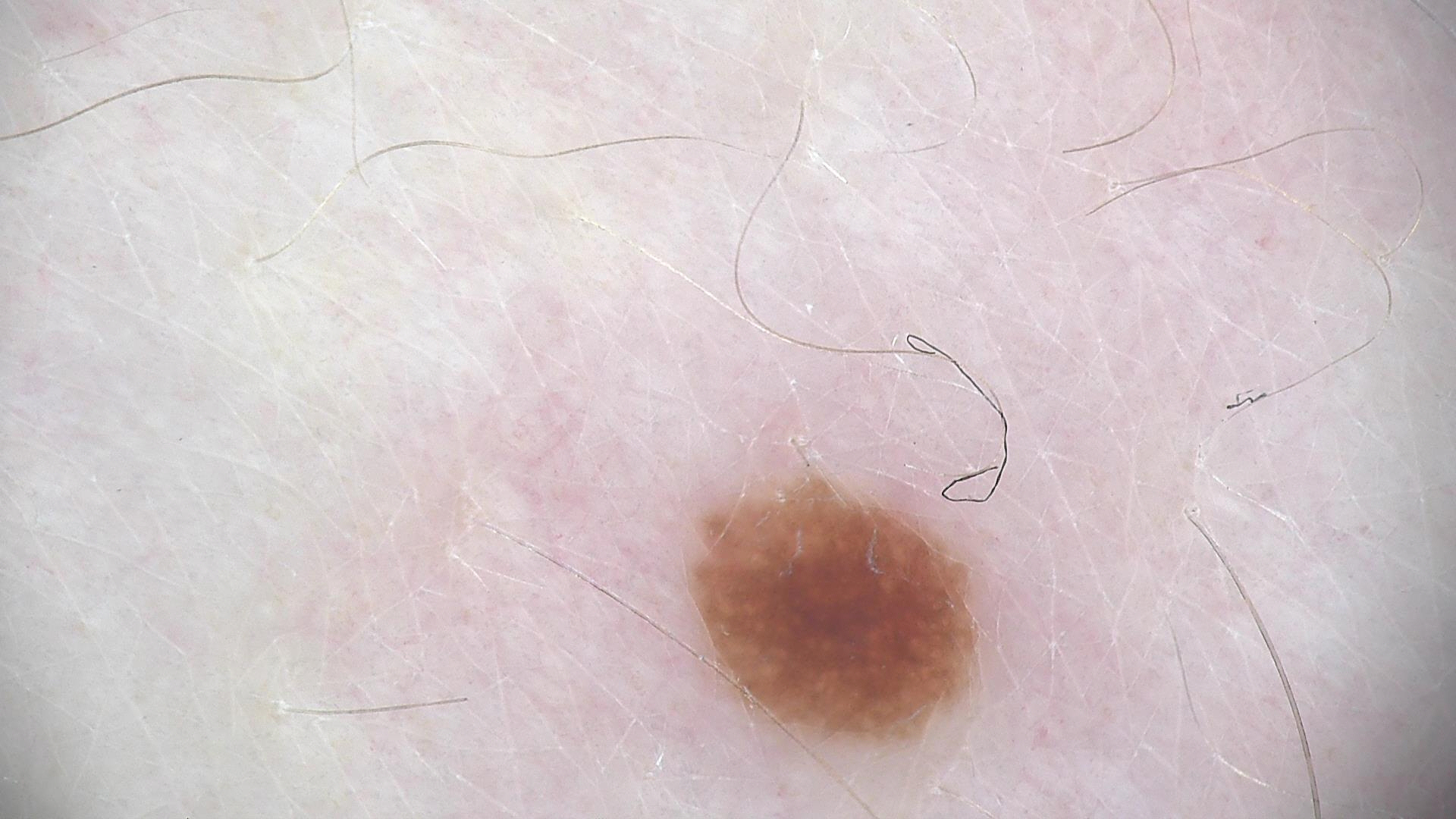Classified as a dysplastic junctional nevus.